A dermoscopic close-up of a skin lesion: 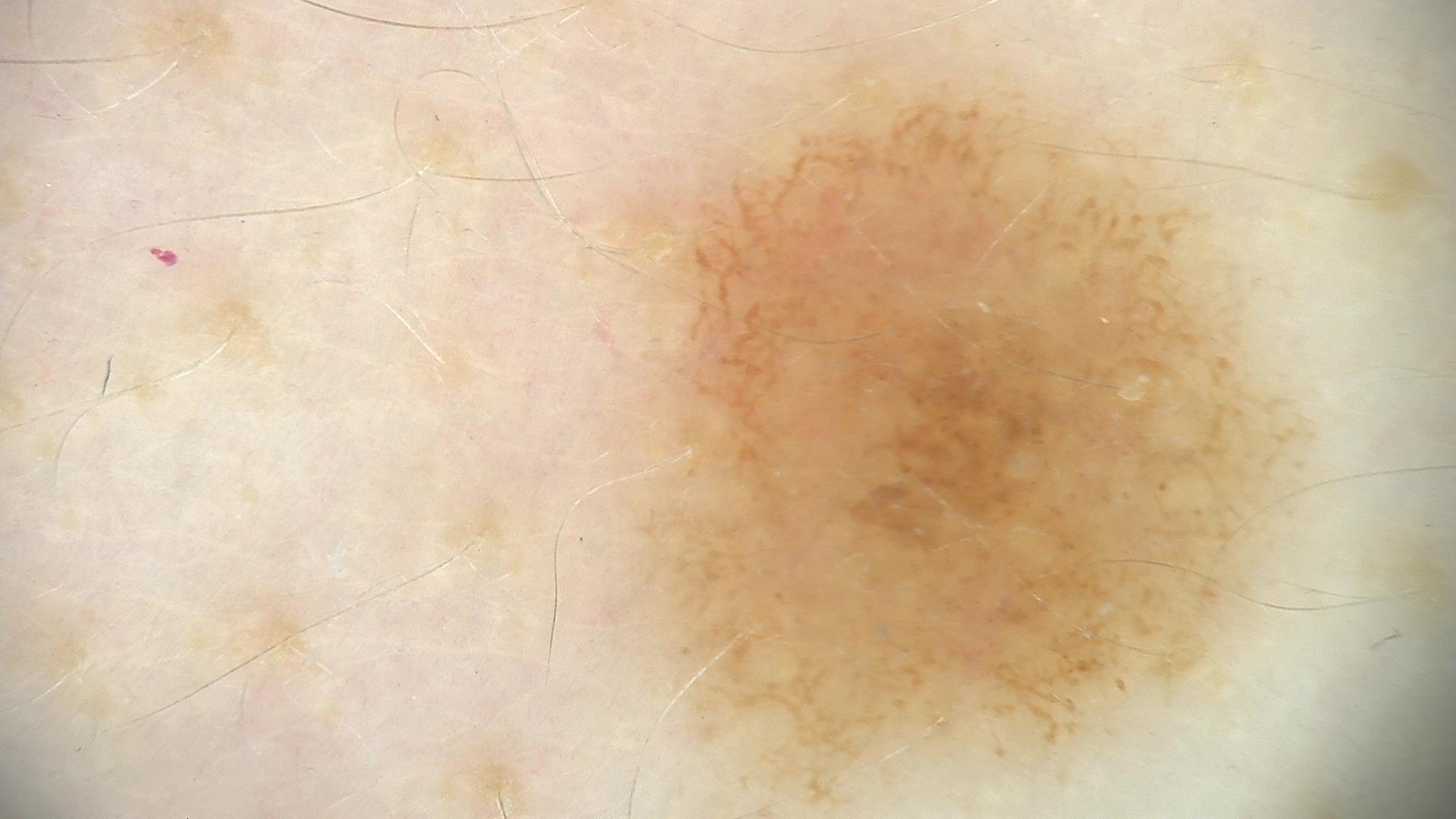The diagnosis was a benign lesion — a dysplastic junctional nevus.